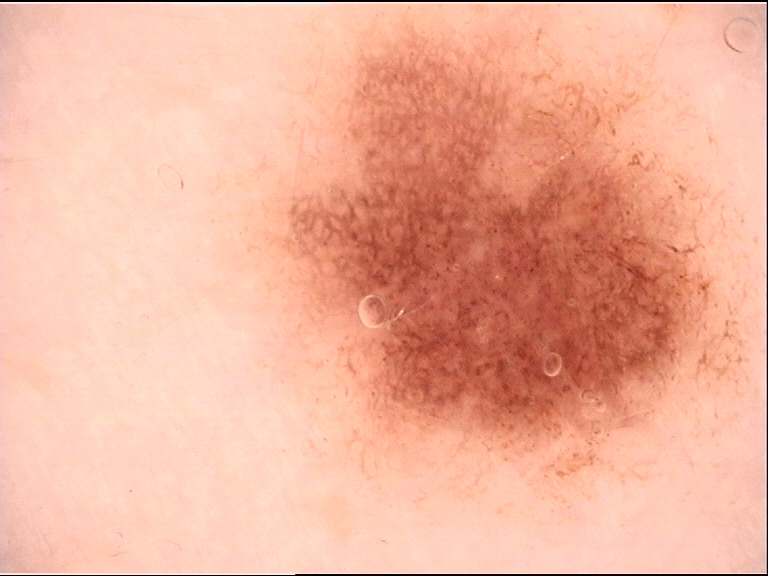The diagnosis was a dysplastic junctional nevus.